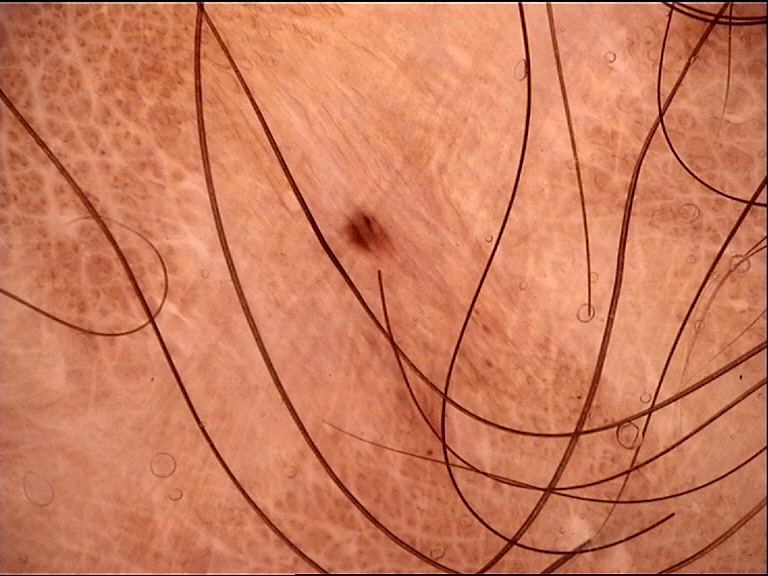diagnostic label = junctional nevus (expert consensus).